A dermoscopy image of a single skin lesion: 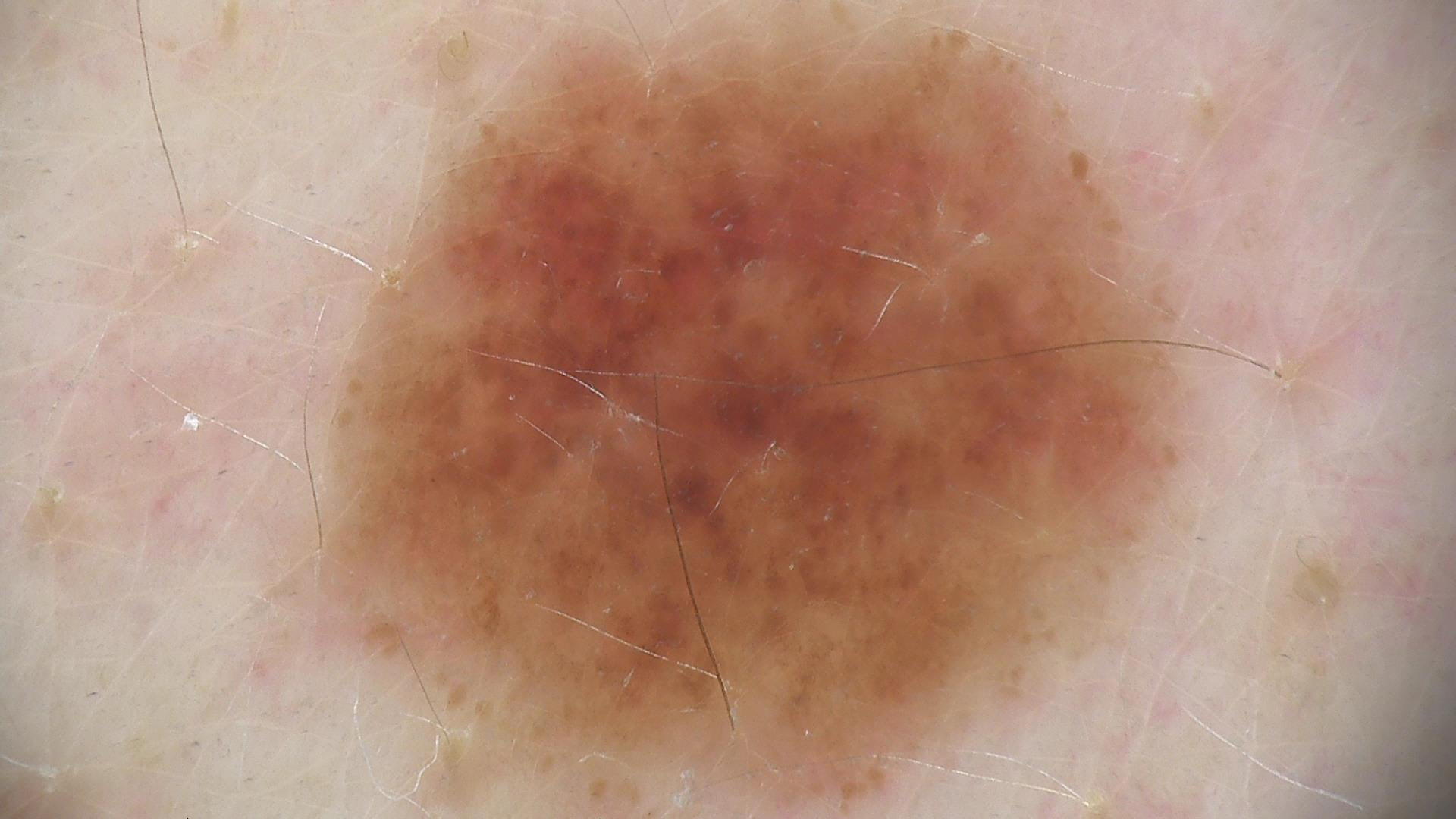Impression: Diagnosed as a dysplastic junctional nevus.